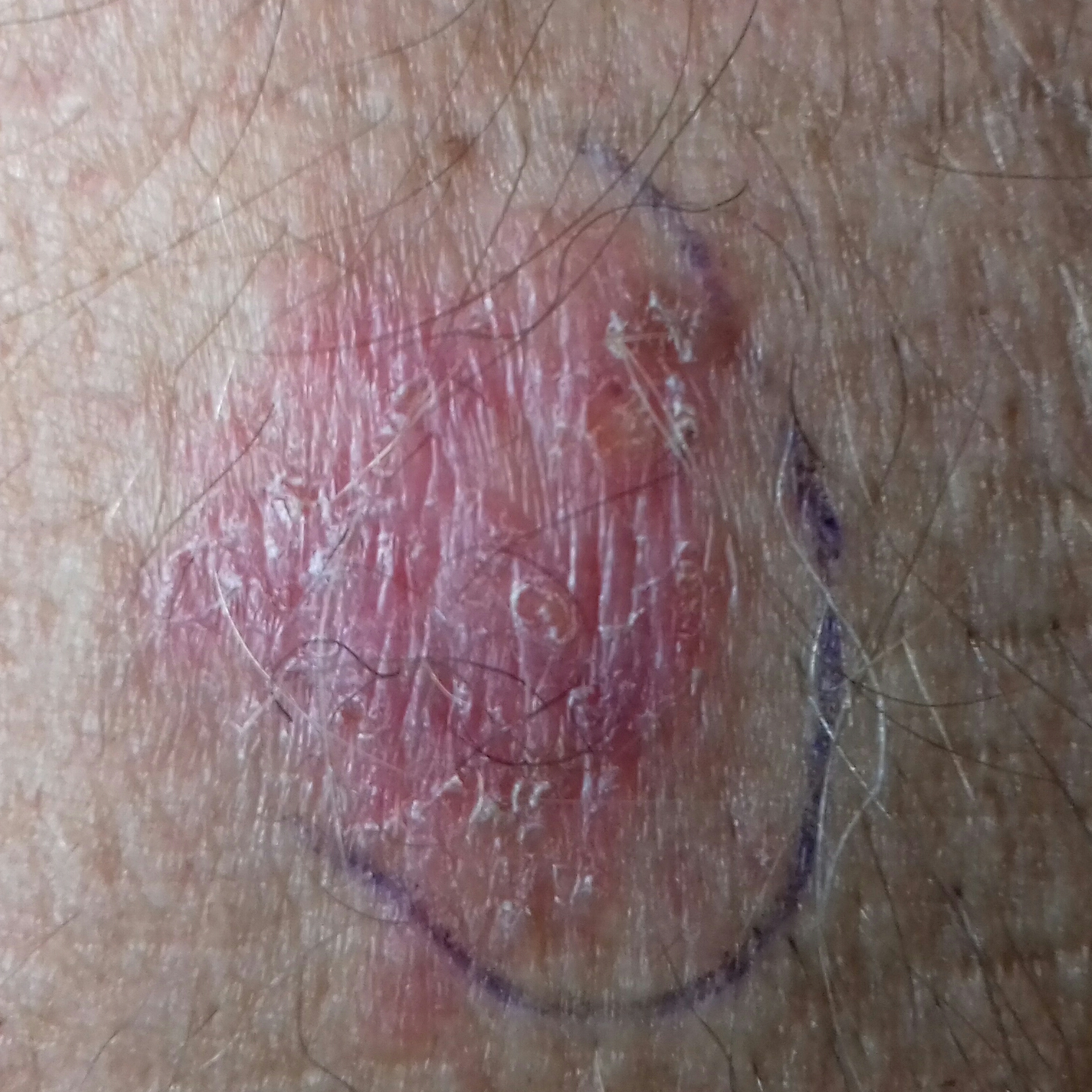Notes:
* imaging: smartphone clinical photo
* risk factors: prior skin cancer (patient or family), pesticide exposure, alcohol use
* site: the face
* size: approx. 10 × 9 mm
* reported symptoms: itching, growth
* pathology: squamous cell carcinoma (biopsy-proven)